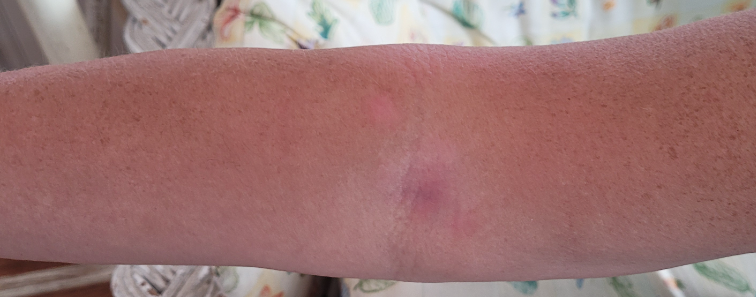On photographic review by a dermatologist: Eczema (primary).